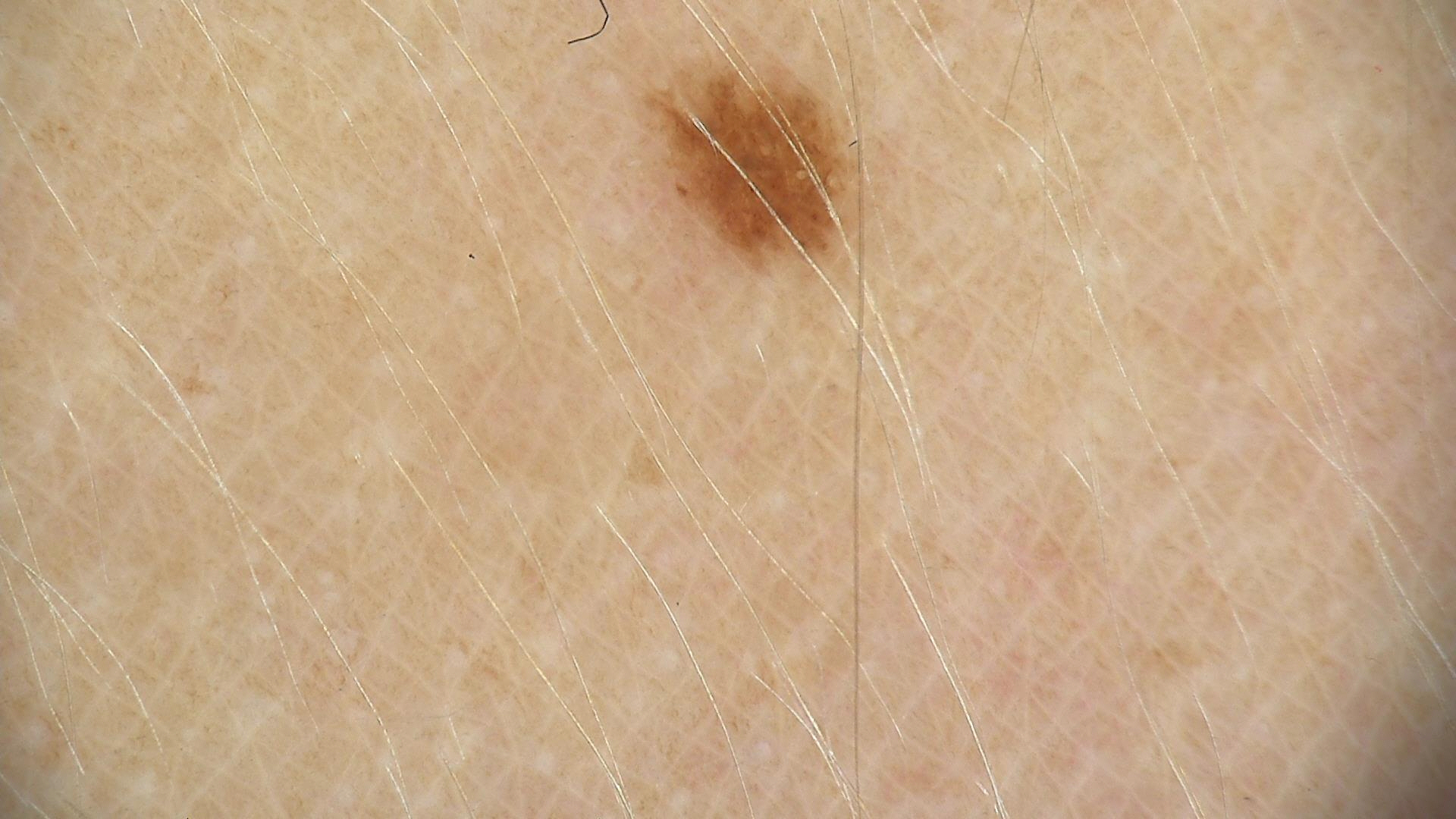{"diagnosis": {"name": "dysplastic junctional nevus", "code": "jd", "malignancy": "benign", "super_class": "melanocytic", "confirmation": "expert consensus"}}